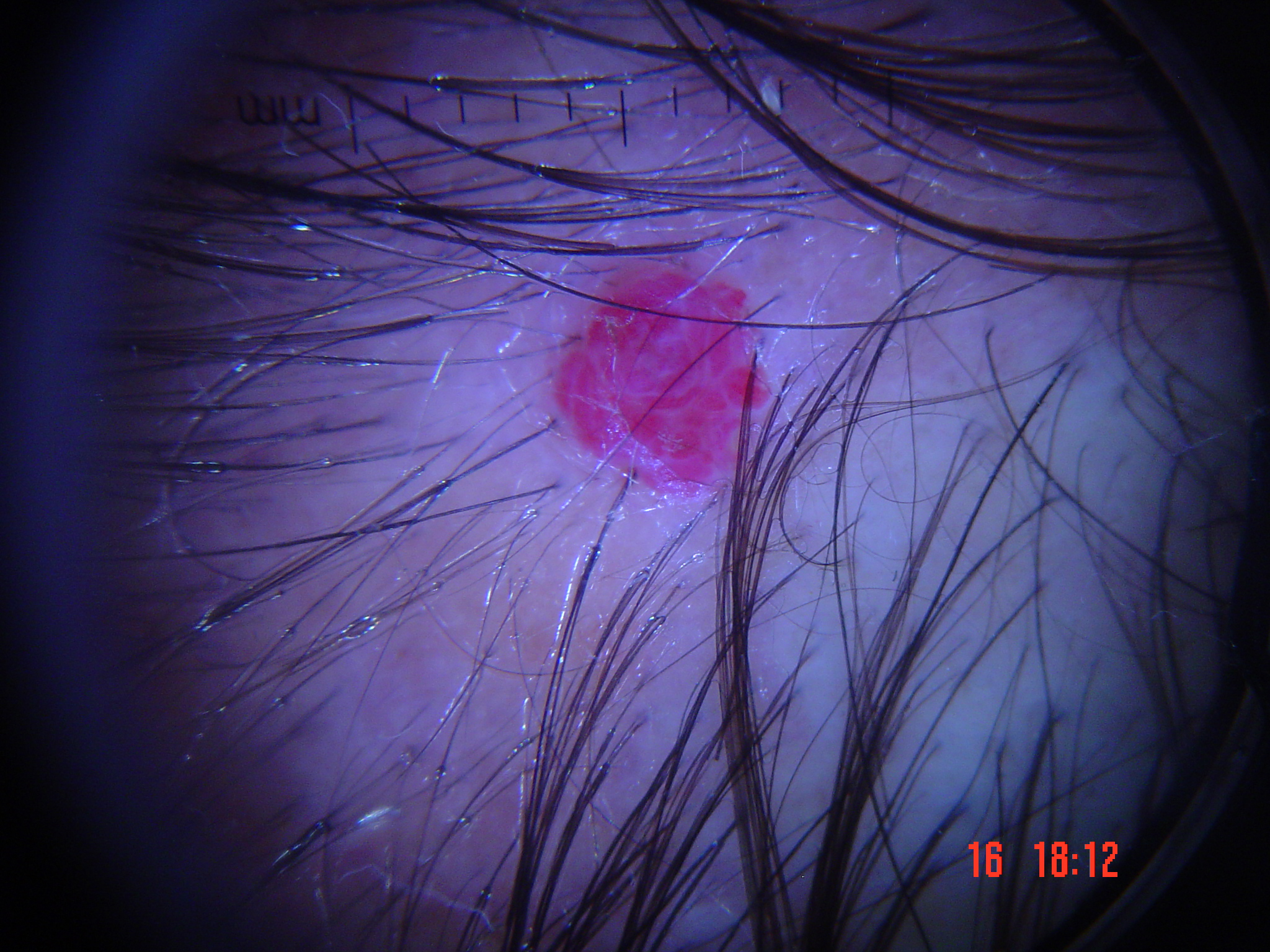Conclusion: Diagnosed as a hemangioma.